The photo was captured at an angle · the lesion involves the front of the torso · the patient is a female aged 50–59 — 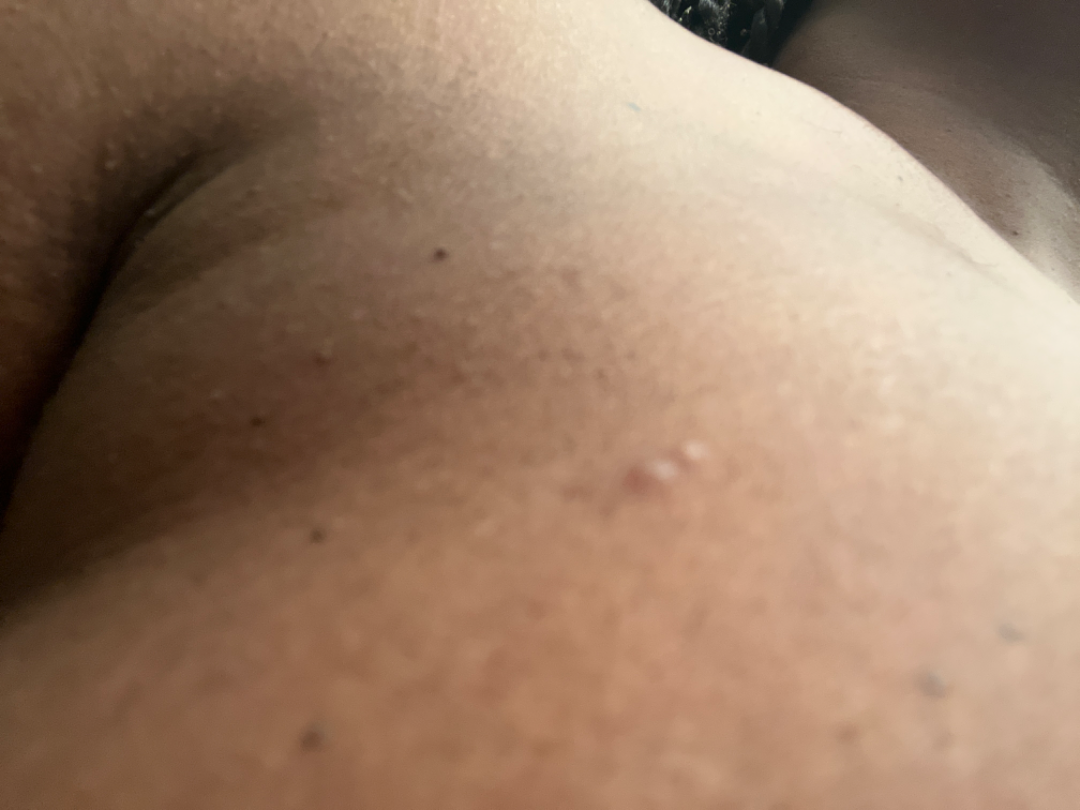Tinea Versicolor and Post-Inflammatory hypopigmentation were considered with similar weight.